A skin lesion imaged with a dermatoscope.
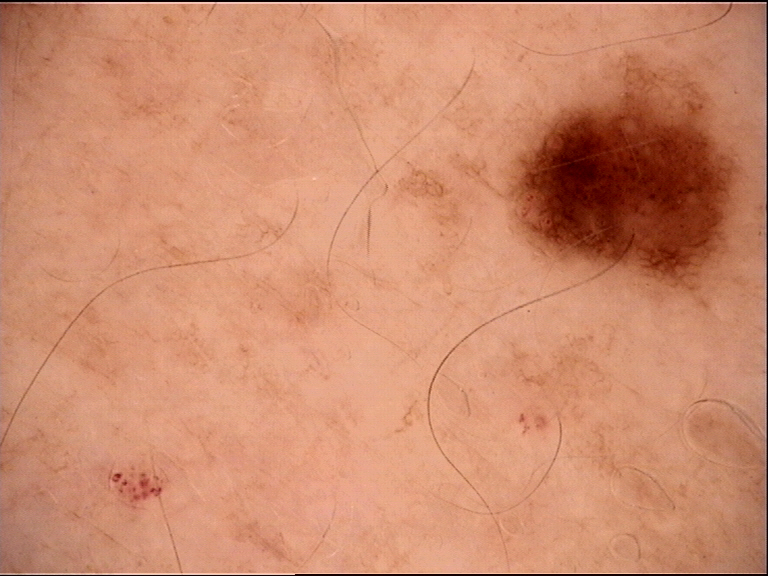Labeled as a benign lesion — a dysplastic junctional nevus.